A dermatoscopic image of a skin lesion.
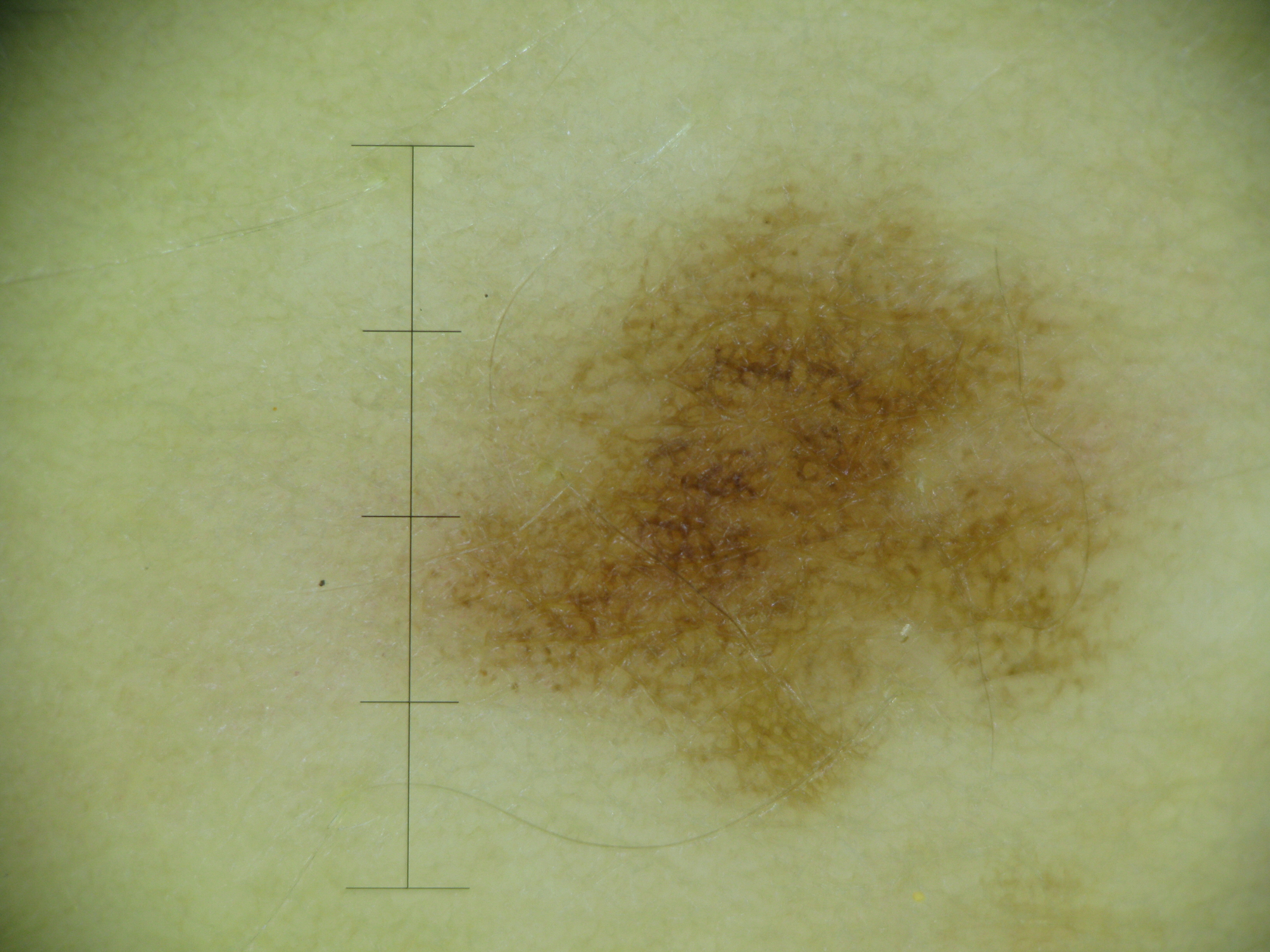Q: What is the diagnosis?
A: dysplastic junctional nevus (expert consensus)